This image was taken at an angle:
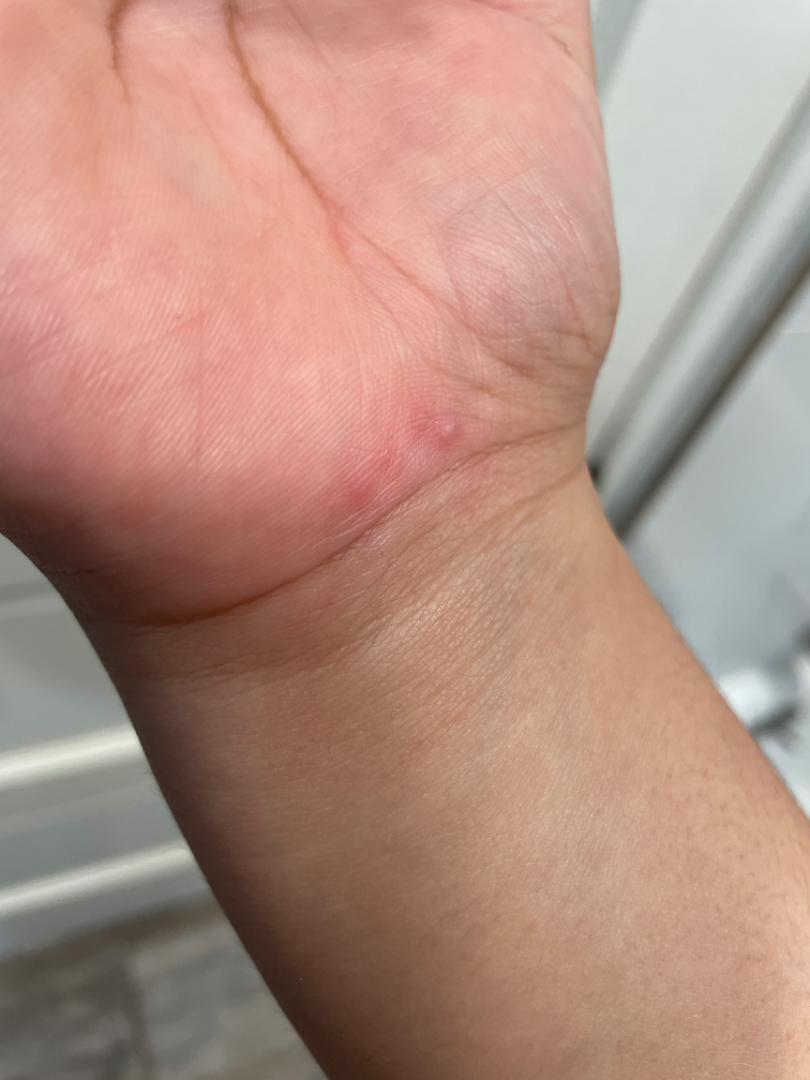| feature | finding |
|---|---|
| skin tone | Fitzpatrick skin type III |
| dermatologist impression | favoring Viral Exanthem; with consideration of Herpes Simplex |